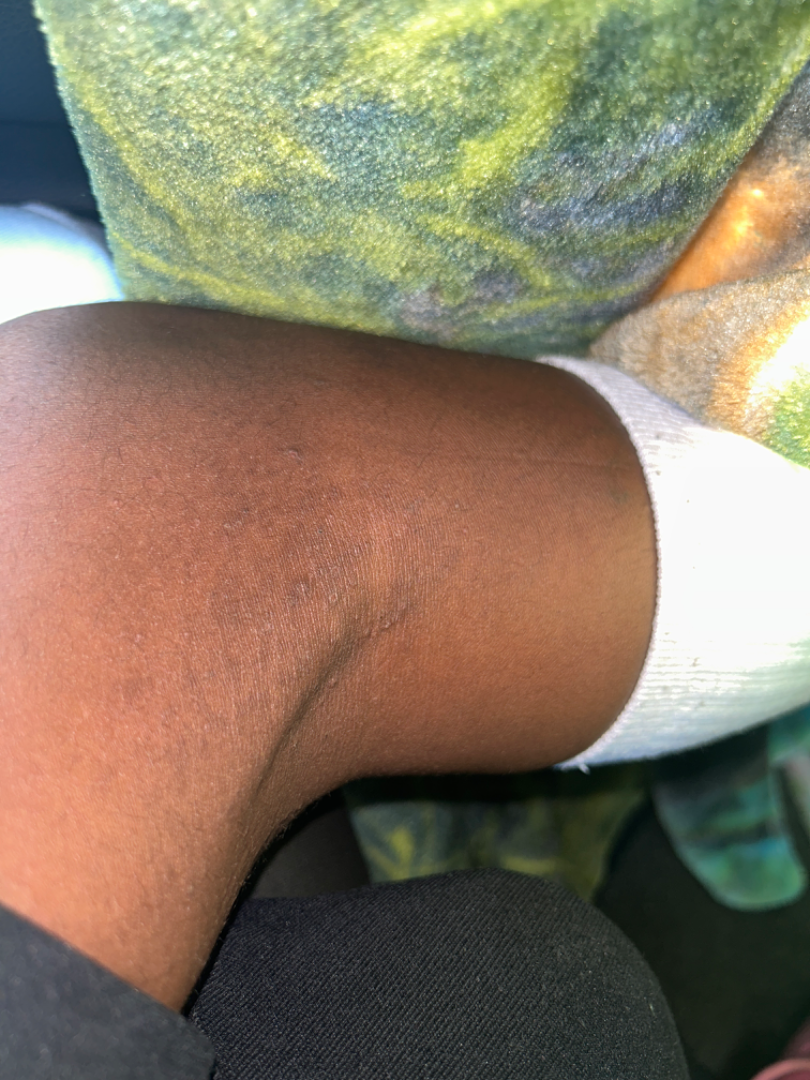Most consistent with Eczema.